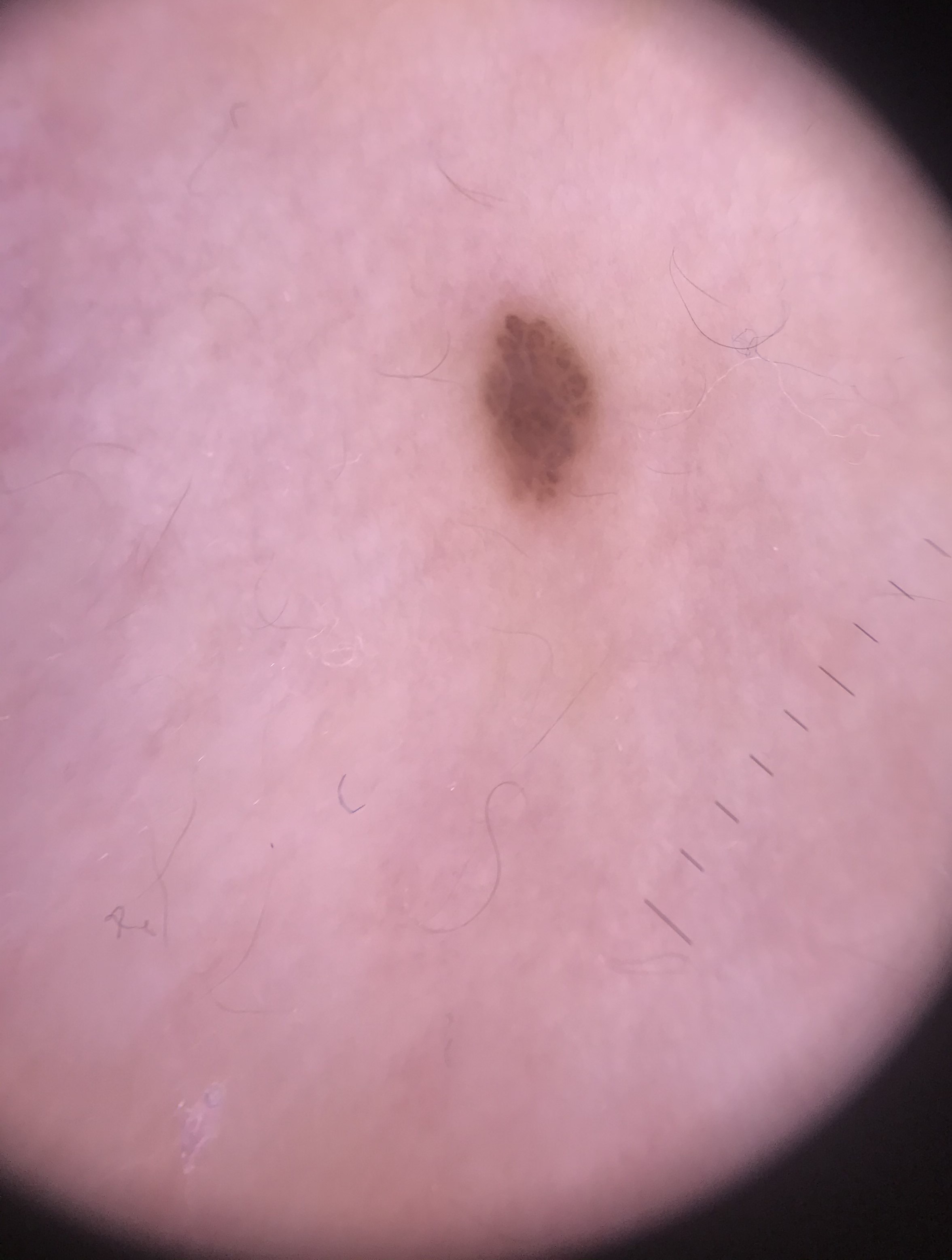assessment: compound nevus (expert consensus).